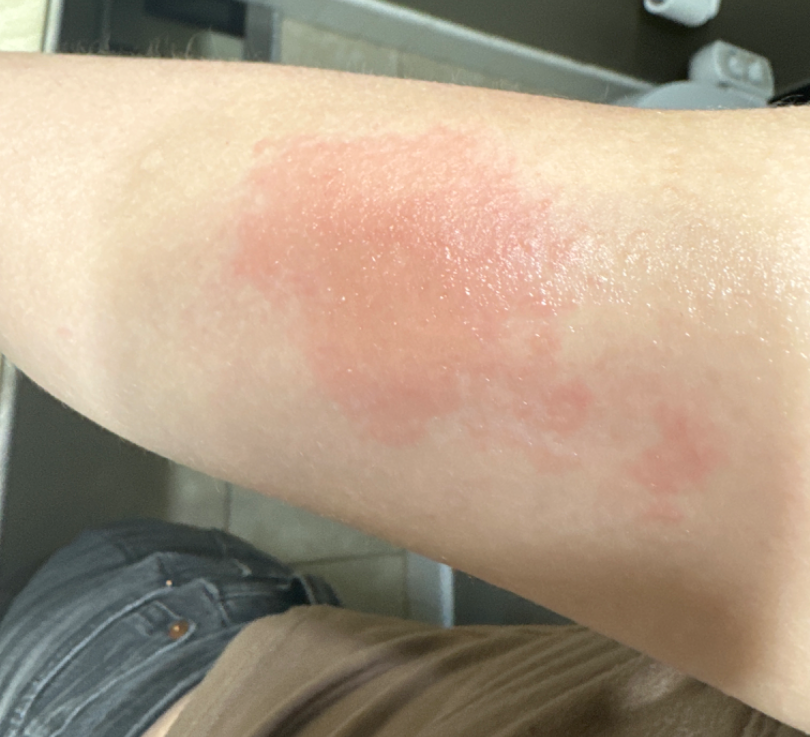| feature | finding |
|---|---|
| photo taken | close-up |
| body site | arm |
| assessment | one reviewing dermatologist: the favored diagnosis is Allergic Contact Dermatitis; also raised was Acute dermatitis, NOS |